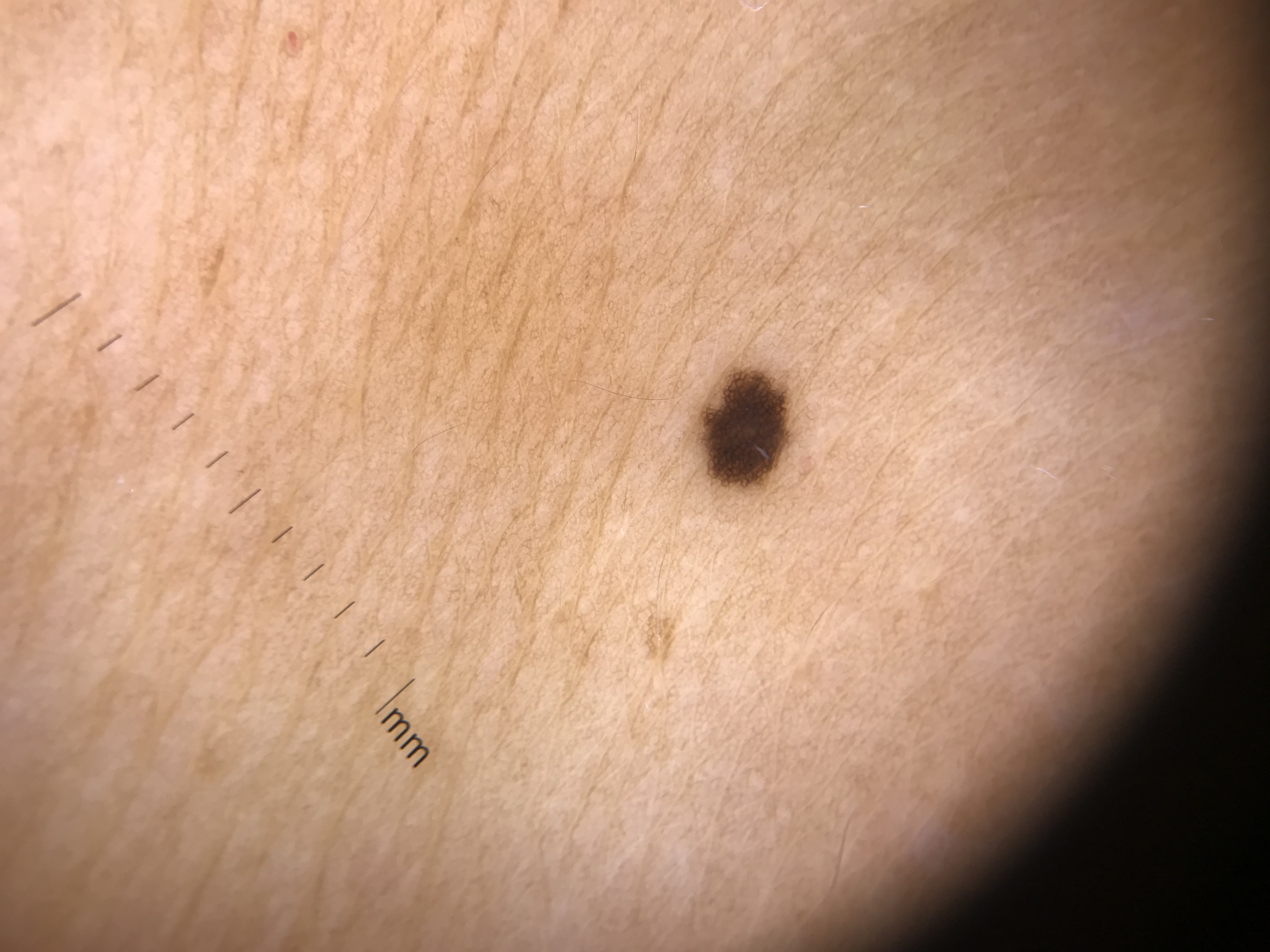Consistent with a junctional nevus.